A close-up photograph. The affected area is the arm. The contributor is a female aged 60–69.
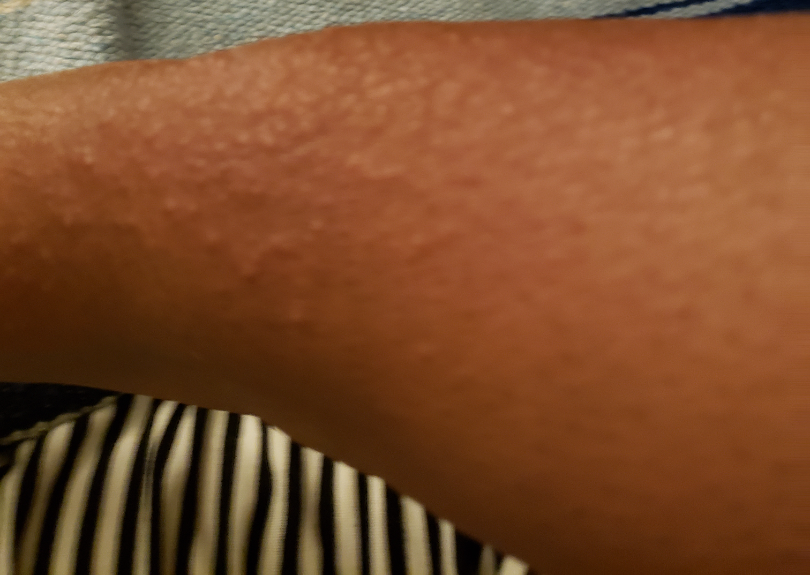constitutional symptoms = none reported | skin tone = Fitzpatrick skin type V; lay graders estimated Monk skin tone scale 4 or 6 | patient describes the issue as = a rash | symptoms = itching | dermatologist impression = Viral Exanthem, Hypersensitivity and Allergic Contact Dermatitis were considered with similar weight.